An image taken at an angle · the affected area is the leg · female patient, age 40–49.
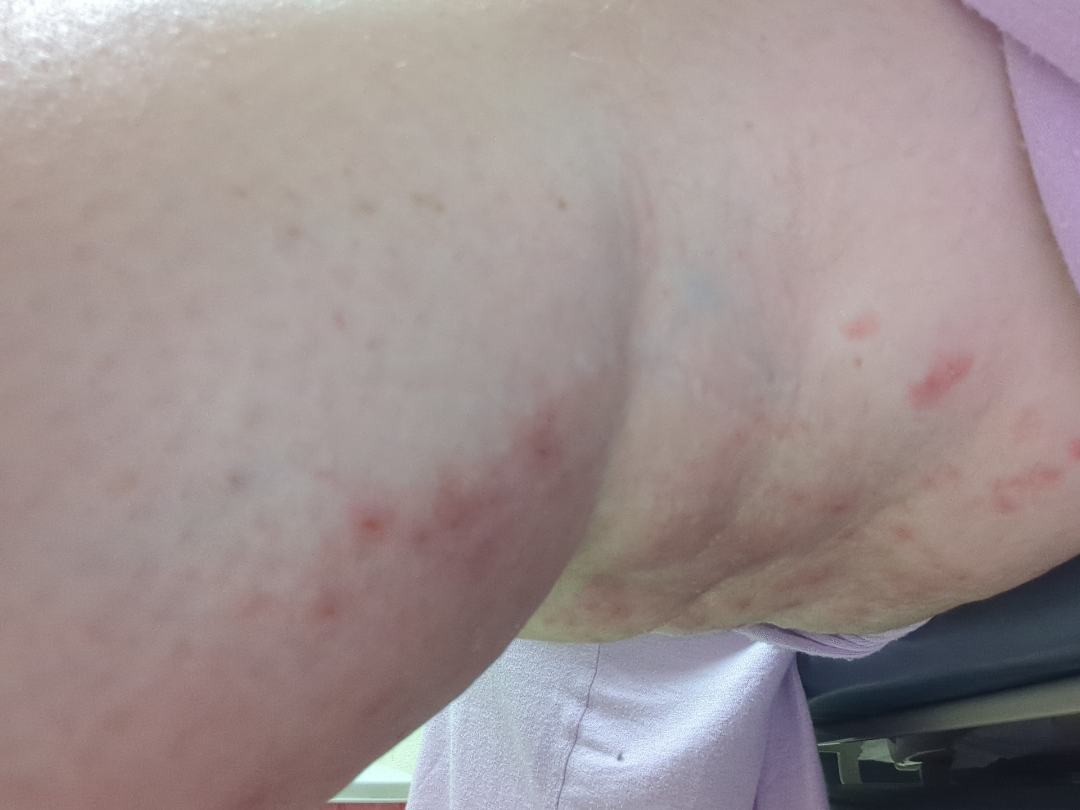Eczema (primary); Folliculitis (possible); Hidradenitis (possible); Irritant Contact Dermatitis (unlikely).